A dermoscopy image of a single skin lesion.
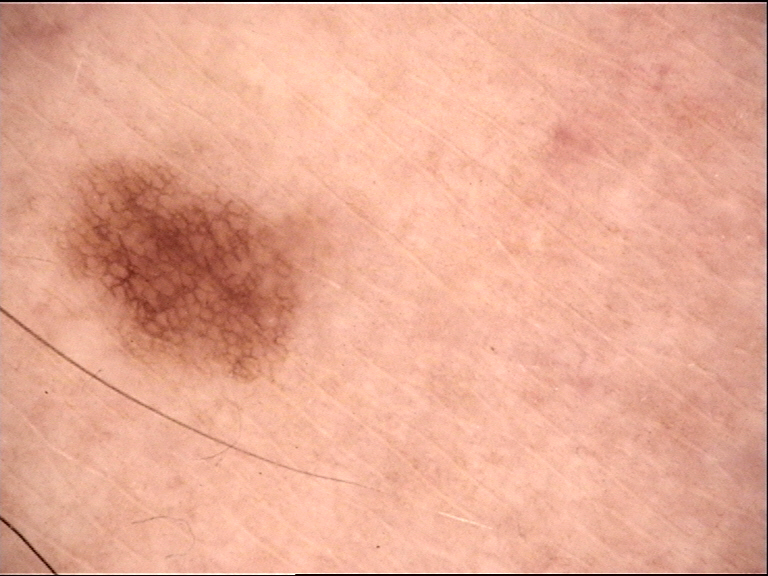label: dysplastic junctional nevus (expert consensus).